A skin lesion imaged with a dermatoscope: 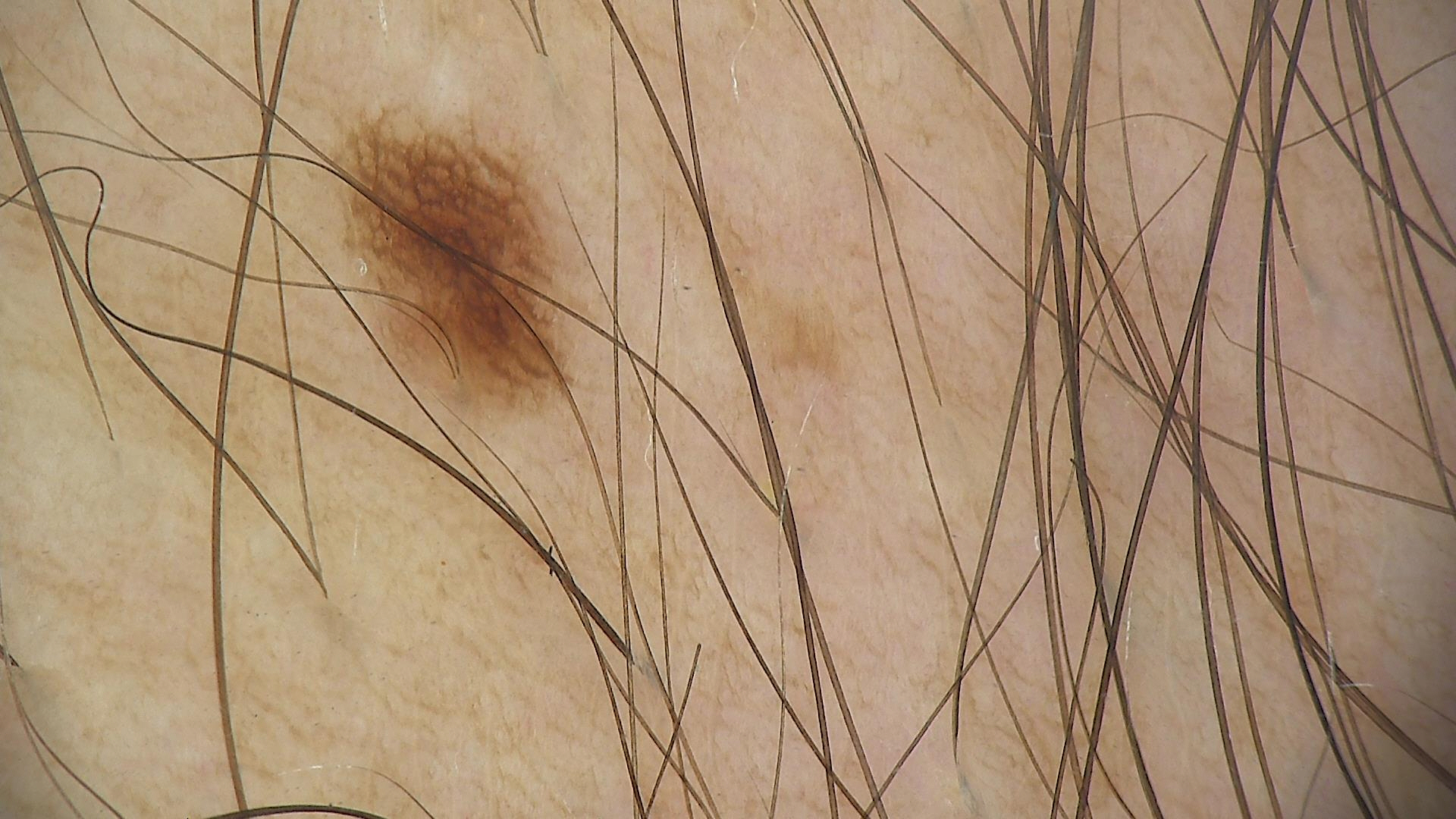diagnosis = dysplastic junctional nevus (expert consensus).